The affected area is the arm; close-up view.
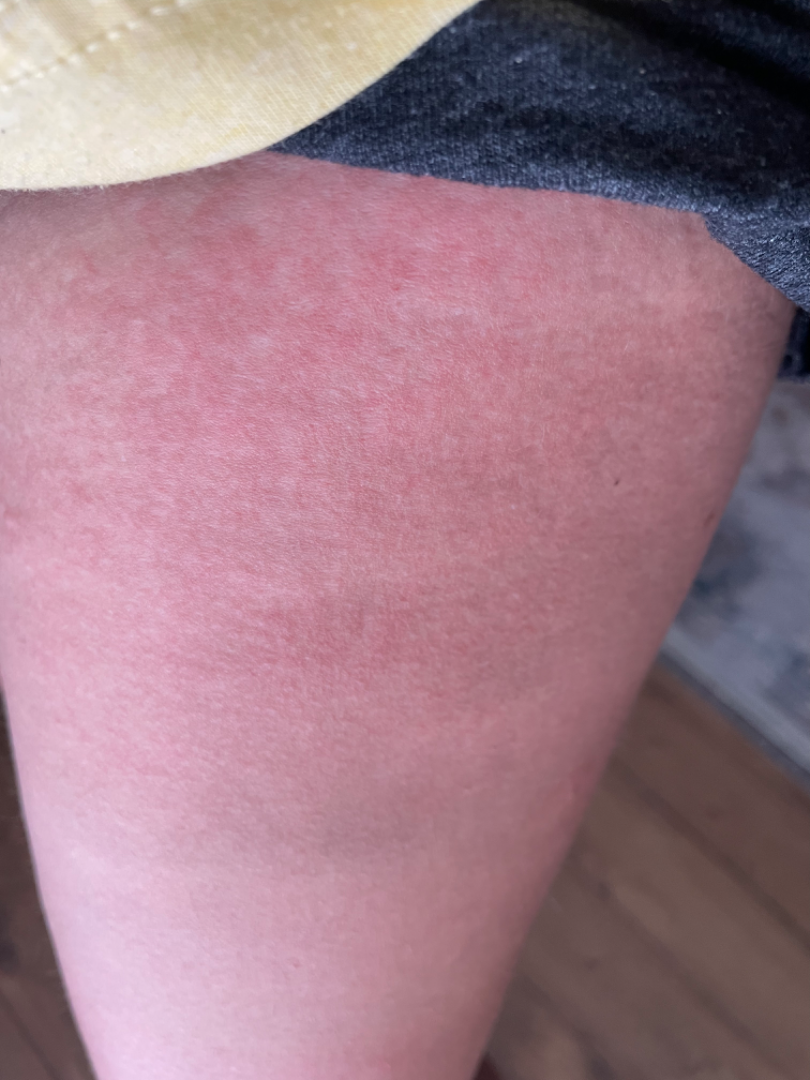Notes:
- impression: Drug Rash (0.33); Viral Exanthem (0.33); Sunburn (0.33)